The patient says their skin tans without first burning. The patient describes having few moles overall. A male subject aged 79.
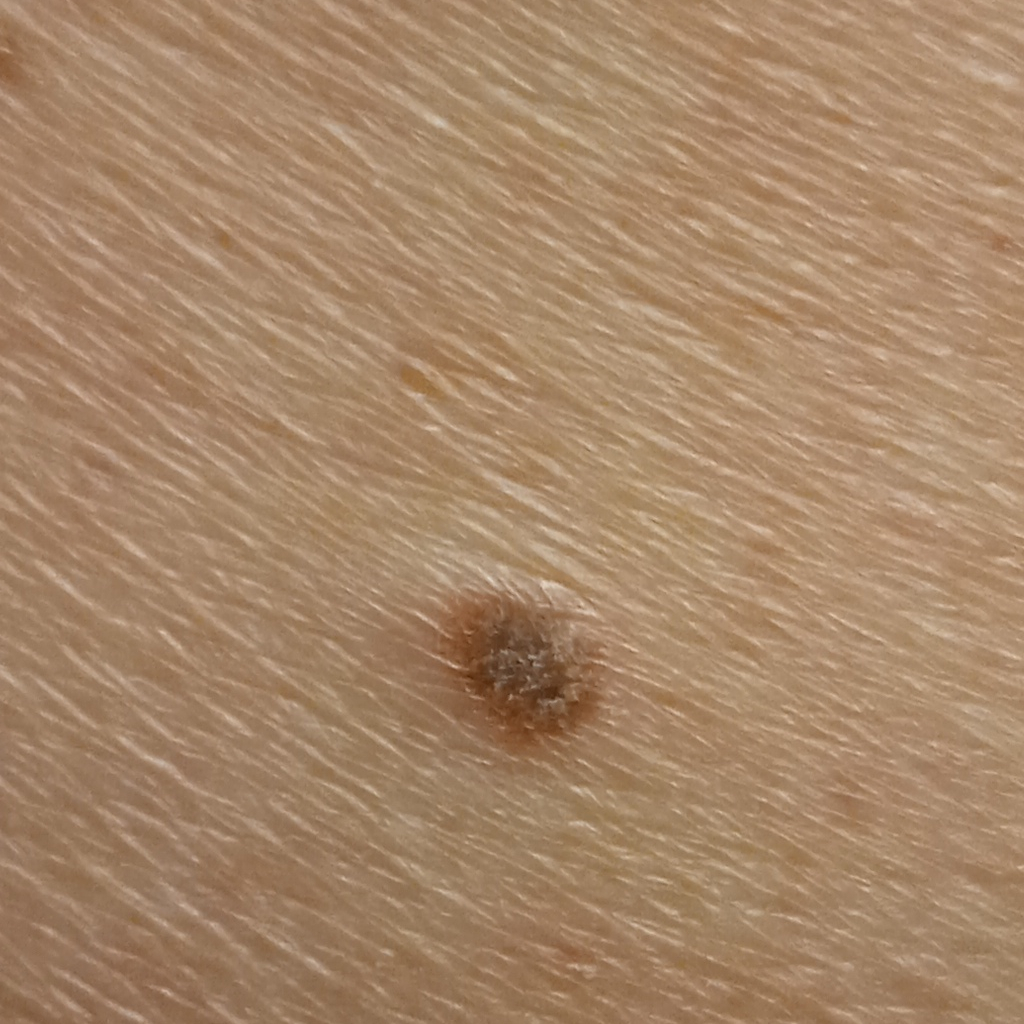Case:
• lesion size: 5.9 mm
• diagnostic label: seborrheic keratosis (dermatologist consensus)